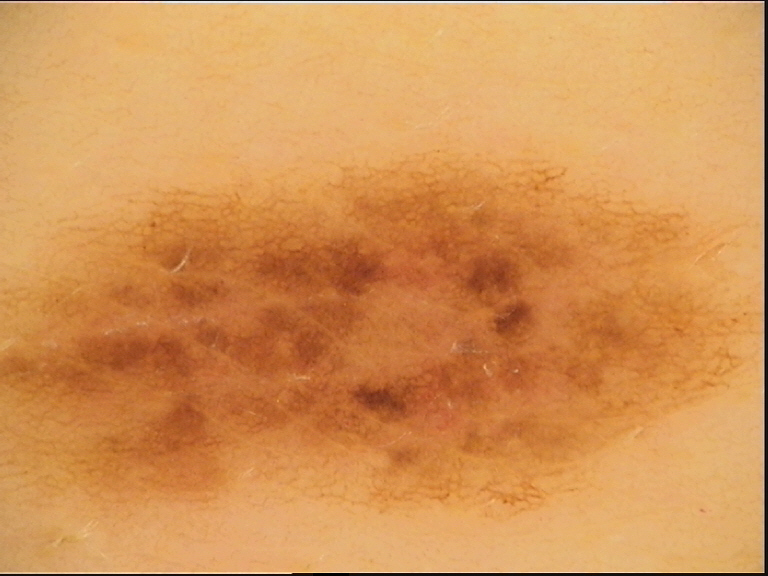Diagnosed as a dysplastic junctional nevus.